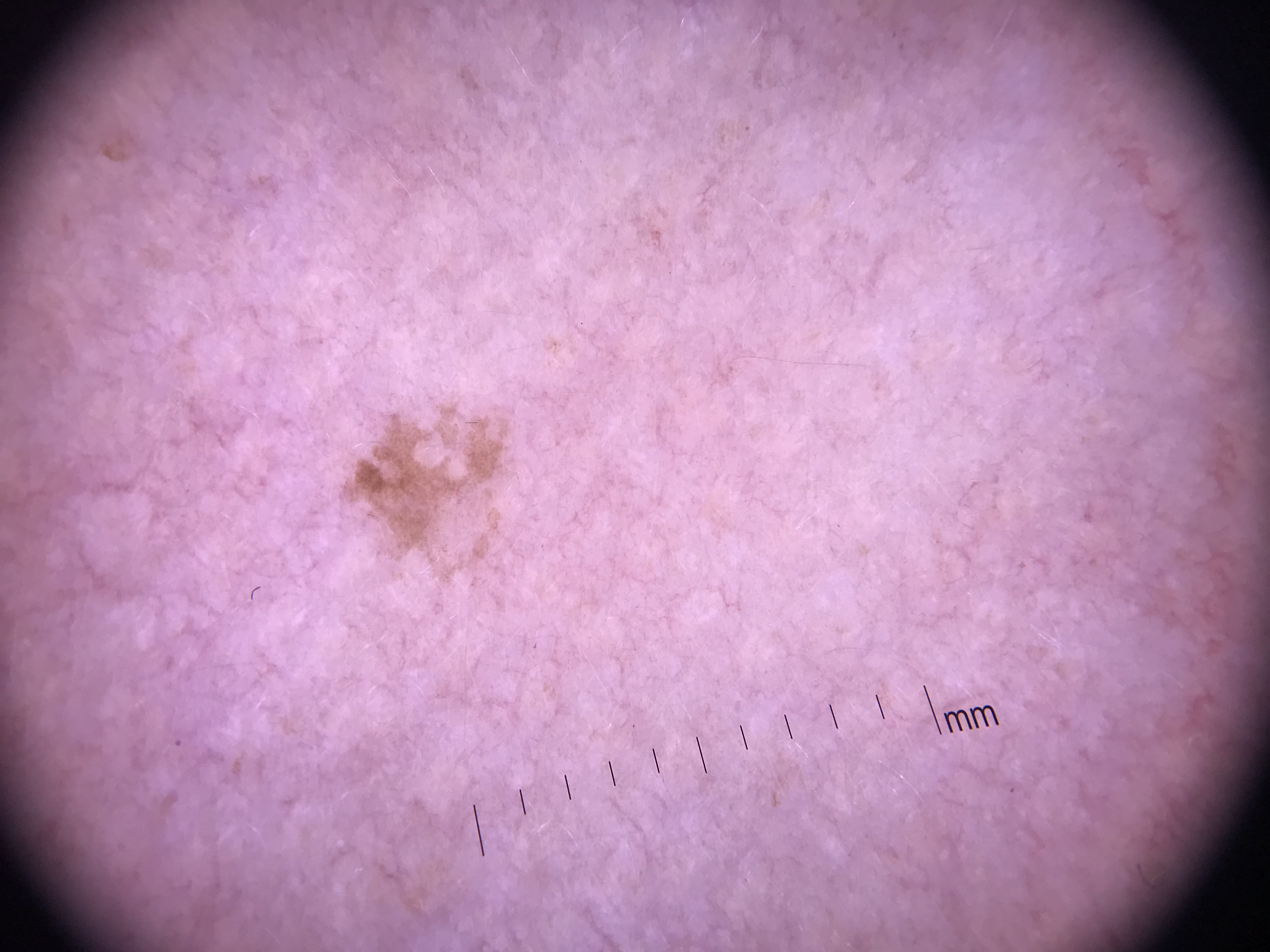A skin lesion imaged with a dermatoscope. Classified as a keratinocytic, benign lesion — a seborrheic keratosis.